A dermoscopy image of a single skin lesion:
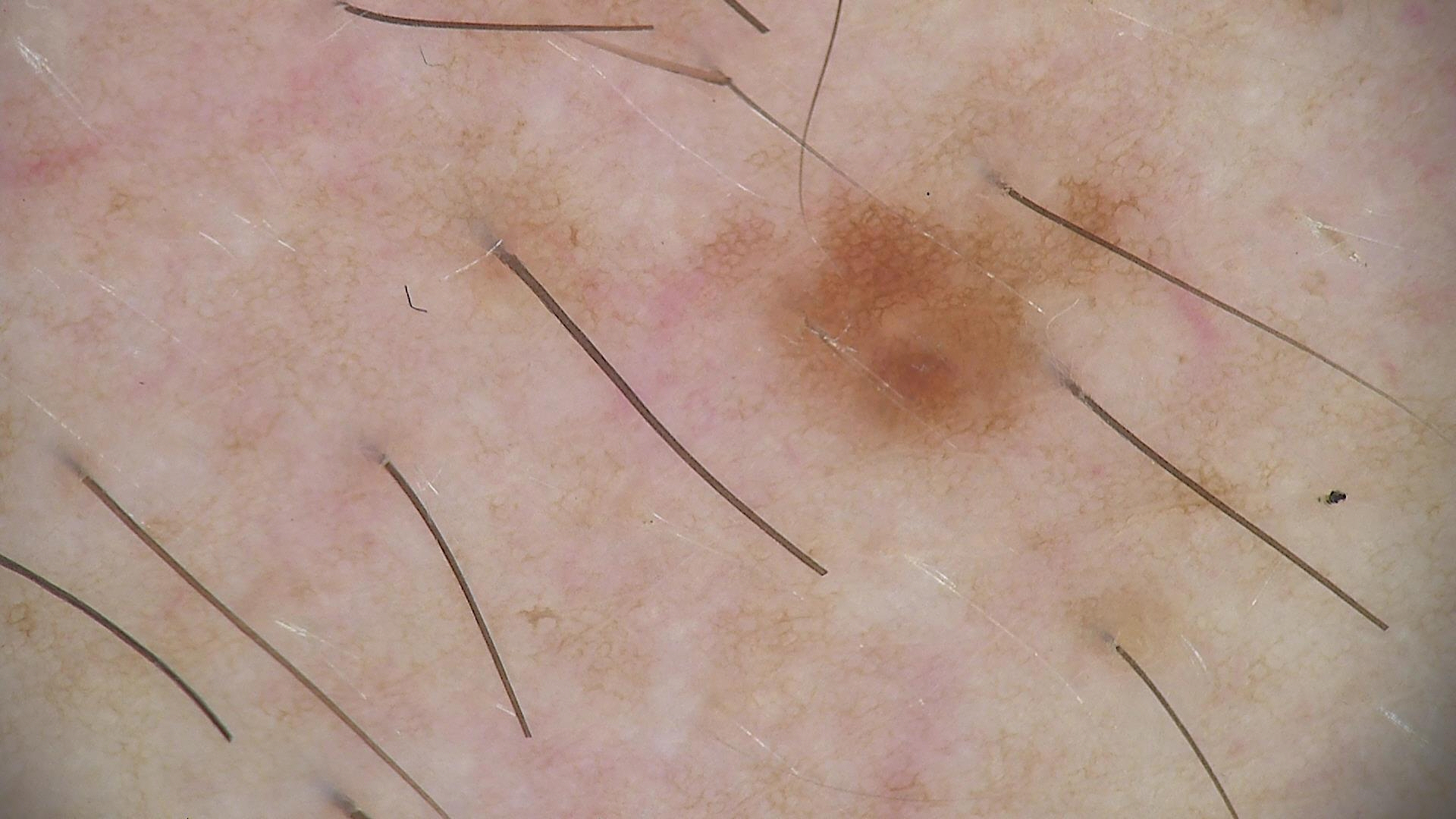Consistent with a benign lesion — a dysplastic junctional nevus.